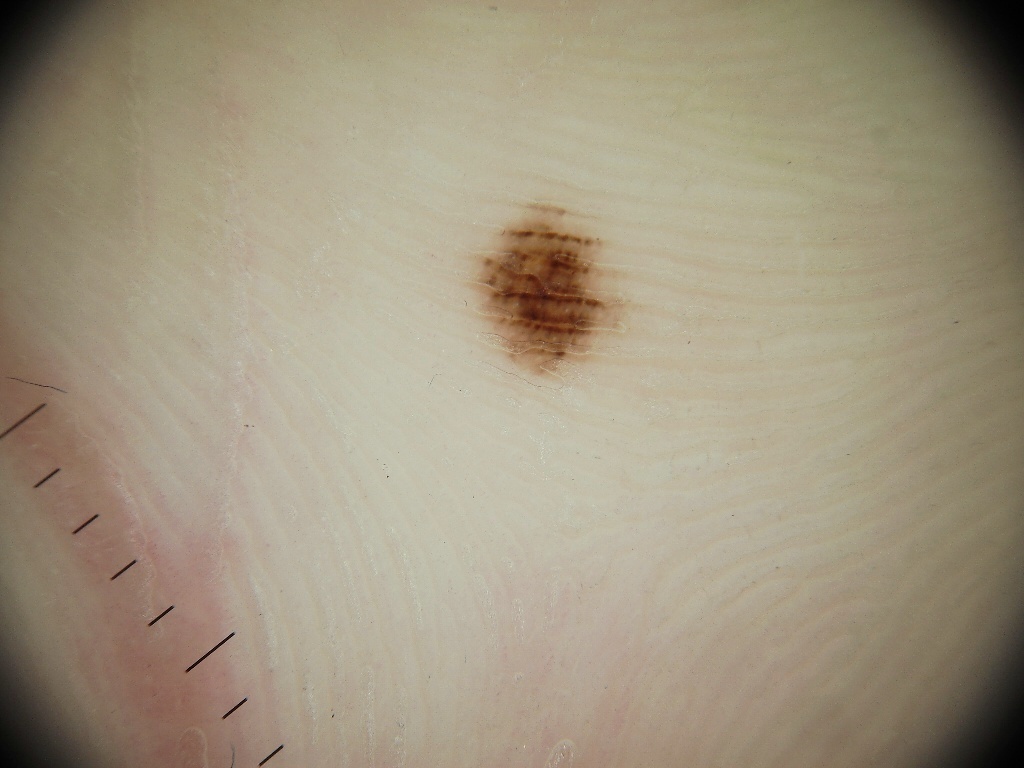A dermoscopic close-up of a skin lesion. A male patient, aged 33 to 37. Dermoscopy demonstrates no milia-like cysts, streaks, pigment network, negative network, or globules. As (left, top, right, bottom), the lesion's extent is <bbox>470, 203, 625, 374</bbox>. The lesion is small relative to the field of view. Expert review diagnosed this as a melanocytic nevus.